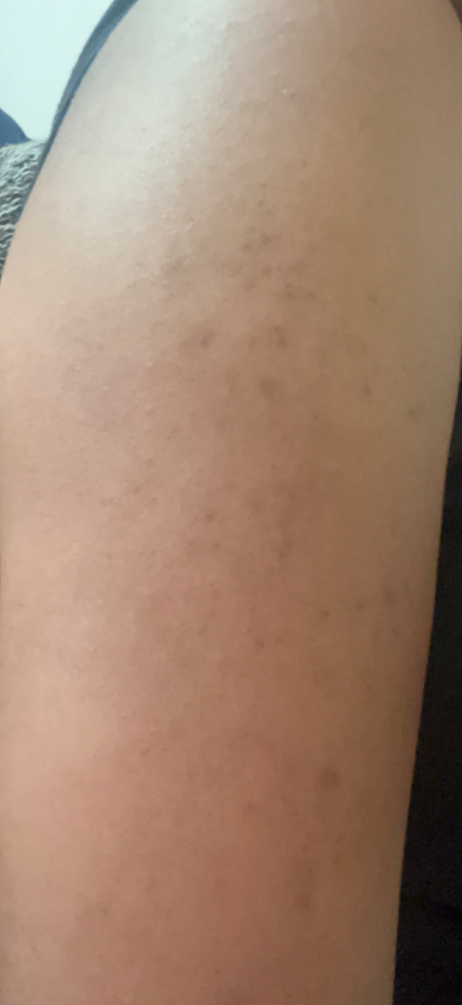<summary>
  <shot_type>close-up</shot_type>
  <duration>more than five years</duration>
  <body_site>arm, back of the hand, back of the torso</body_site>
  <symptoms>itching, bothersome appearance</symptoms>
  <texture>raised or bumpy</texture>
  <patient>female, age 18–29</patient>
  <differential>
    <leading>Keratosis pilaris</leading>
  </differential>
</summary>